A skin lesion imaged with a dermatoscope · the patient reports no personal history of cancer and no sunbed use · imaged for a research study, with no referral diagnosis recorded: 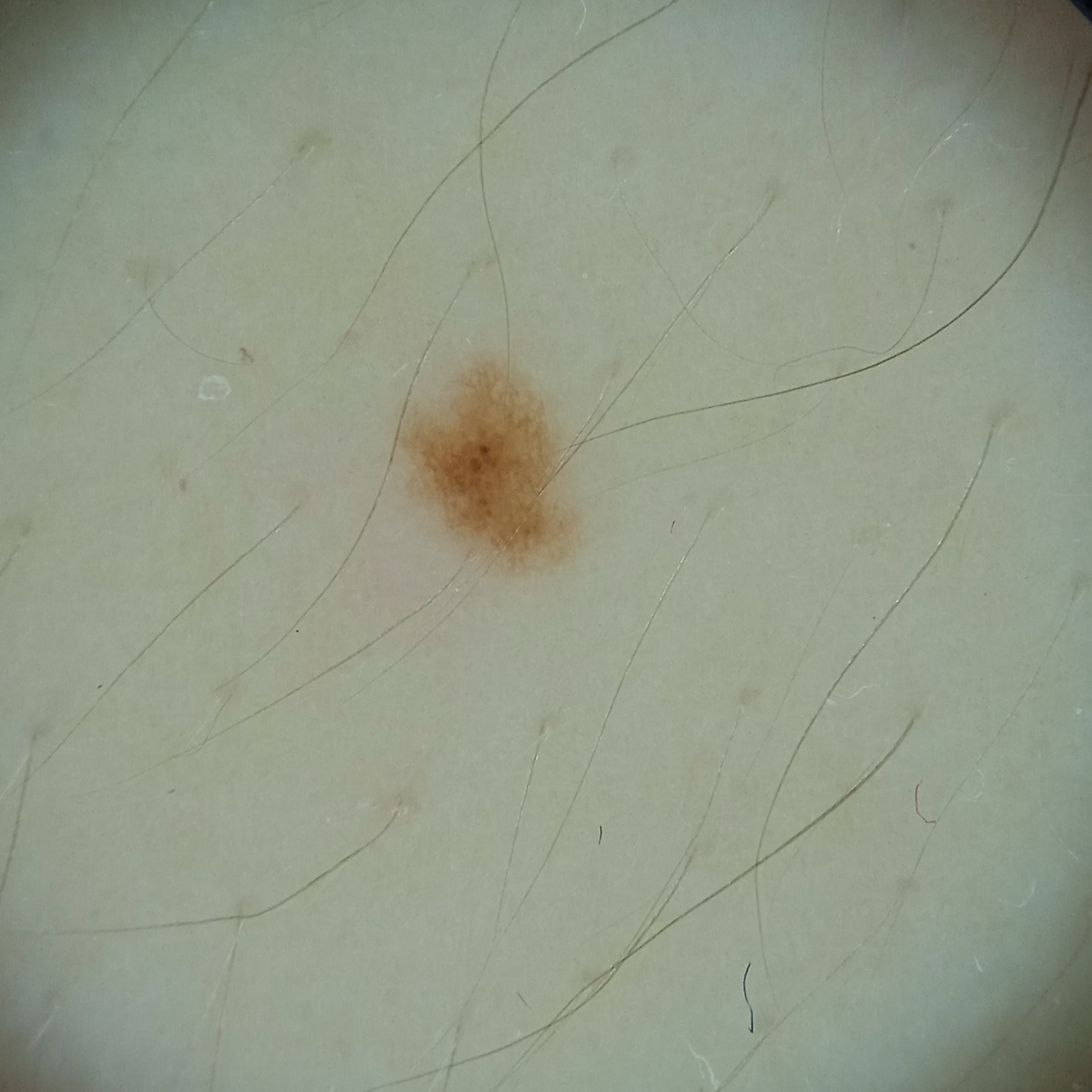Four dermatologists reviewed the lesion; the consensus was a melanocytic nevus; the reviewers were fairly confident.